The subject is a male about 35 years old. This is a dermoscopic photograph of a skin lesion: 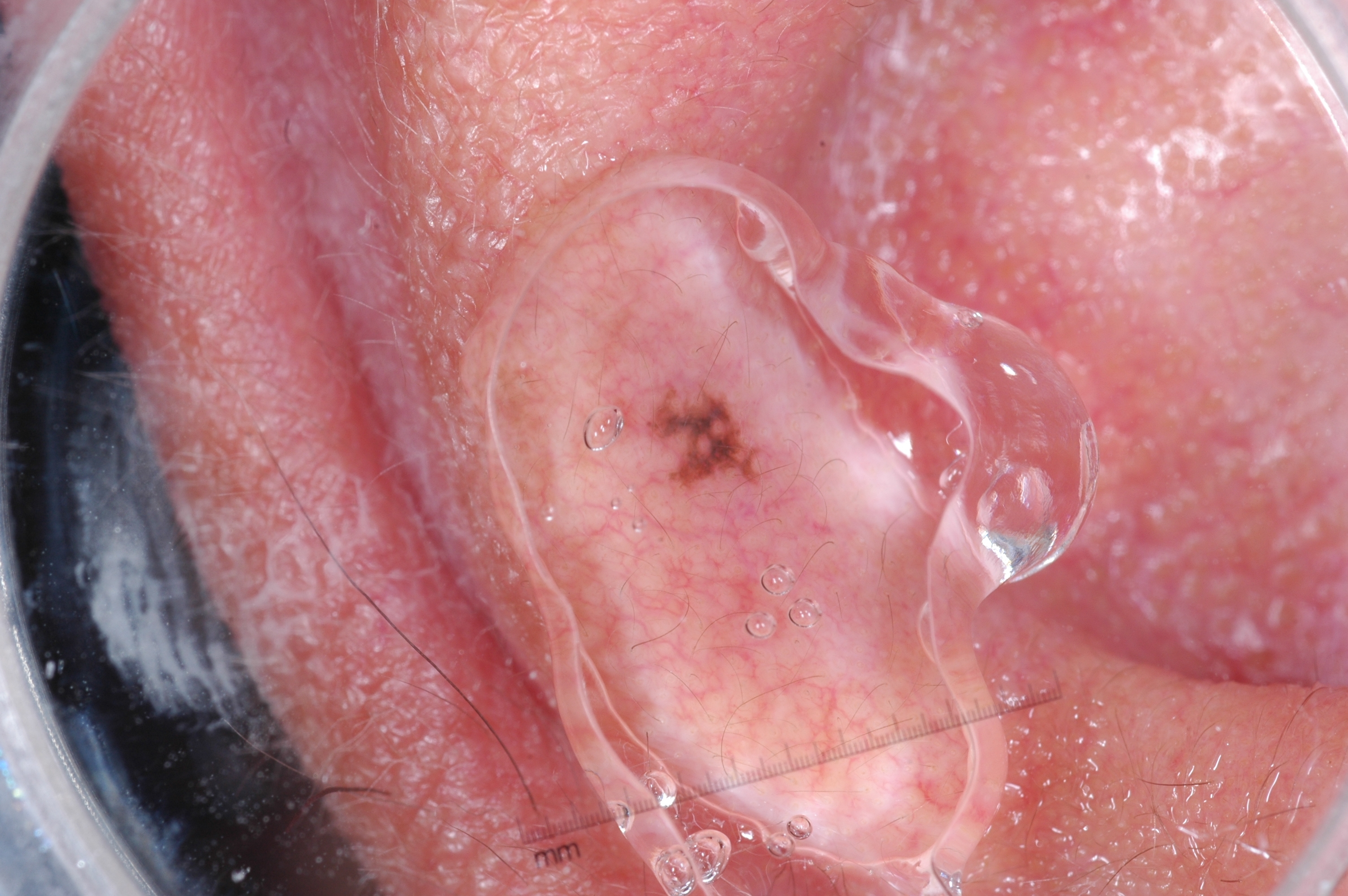Q: Which dermoscopic features are absent?
A: pigment network, negative network, streaks, and milia-like cysts
Q: Where is the lesion in the image?
A: left=646, top=381, right=780, bottom=493
Q: What is the diagnosis?
A: a melanocytic nevus